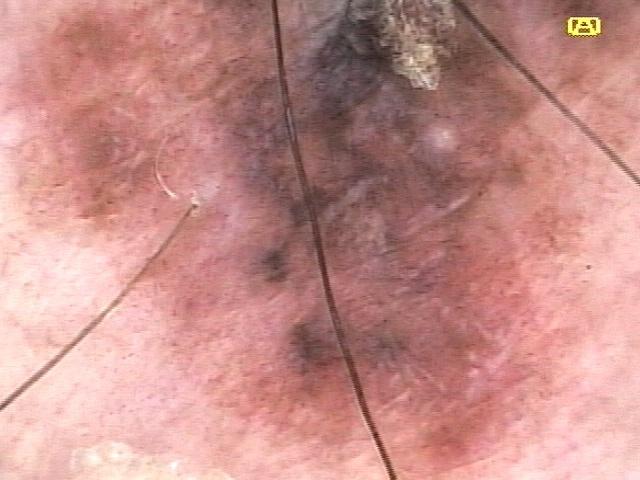Recorded as Fitzpatrick phototype II.
The lesion was found on a lower extremity.
Histopathological examination showed a skin cancer — a melanoma.